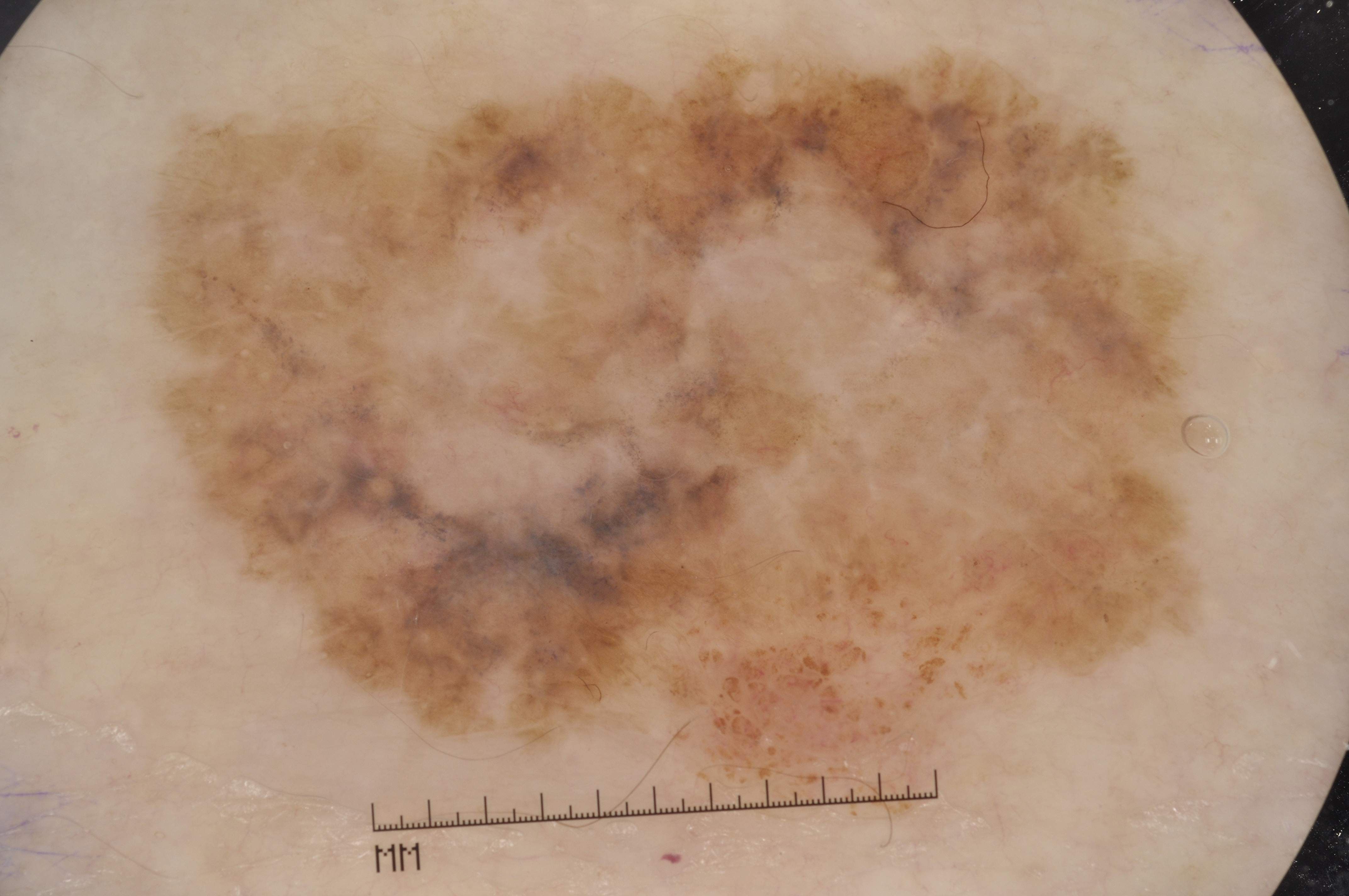image type = dermatoscopic image of a skin lesion; lesion extent = large; absent dermoscopic findings = streaks, milia-like cysts, negative network, and pigment network; lesion location = <box>137, 49, 1212, 833</box>; diagnostic label = a melanoma, a skin cancer.